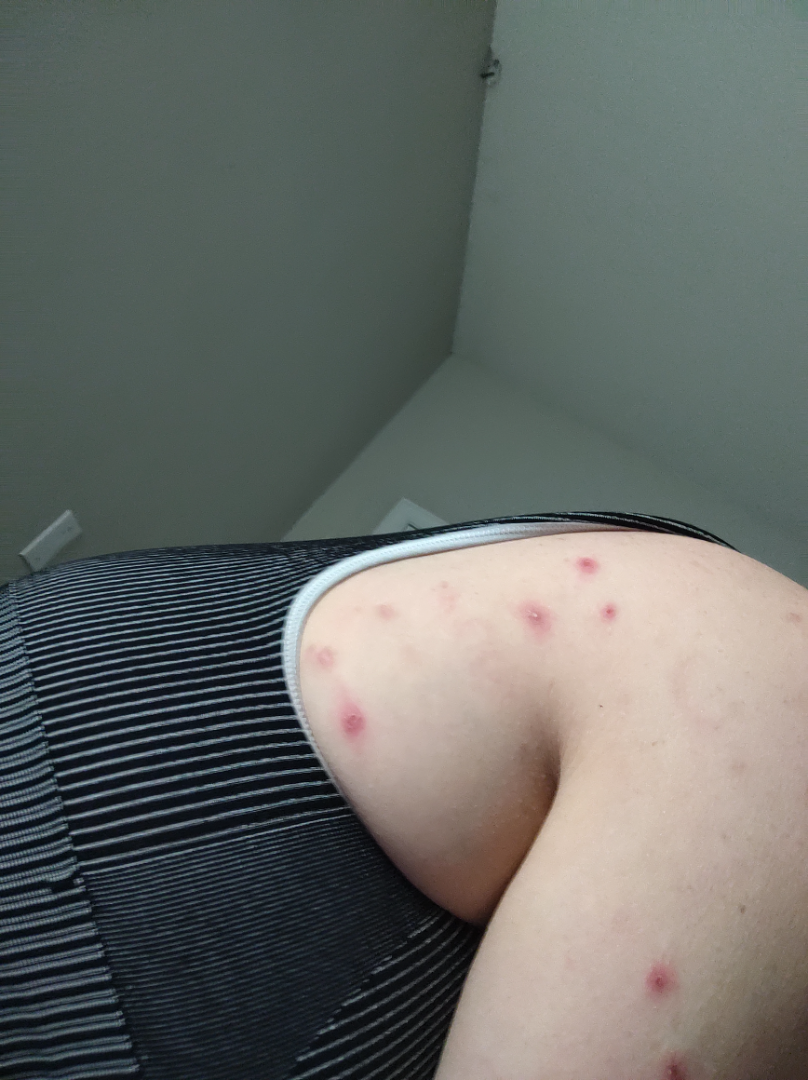This is a close-up image.
On photographic review, favoring Inflicted skin lesions; possibly Insect Bite; less likely is Skin infection.